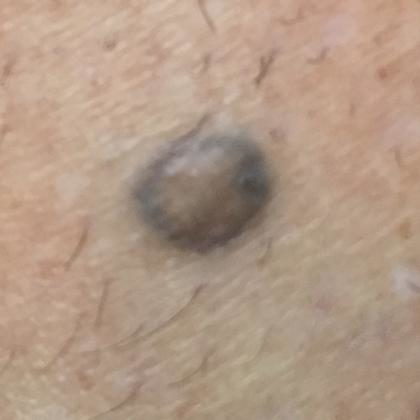Notes:
• subject: female, 50 years of age
• exposure history: tobacco use, prior malignancy (patient or family), no alcohol use
• imaging: clinical photo
• FST: III
• lesion size: approx. 5 × 3 mm
• reported symptoms: elevation, growth / no pain, no change in appearance
• assessment: nevus (clinical consensus)